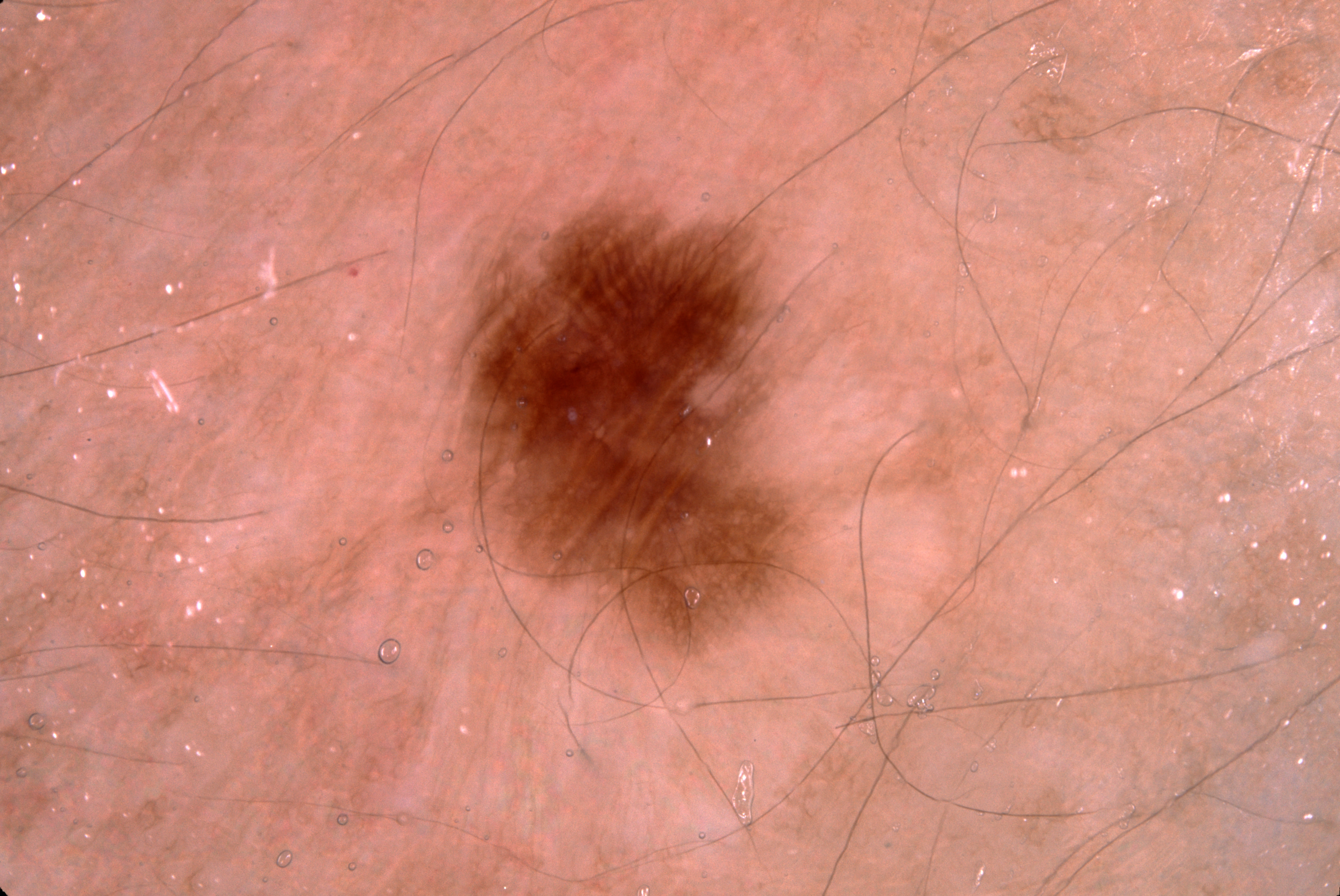Findings: This is a dermoscopic photograph of a skin lesion. Dermoscopic assessment notes pigment network; no negative network, streaks, or milia-like cysts. The visible lesion spans x1=471 y1=210 x2=806 y2=644. The lesion takes up about 9% of the image. Conclusion: The diagnostic assessment was a melanocytic nevus, a benign lesion.